A skin lesion imaged with a dermatoscope:
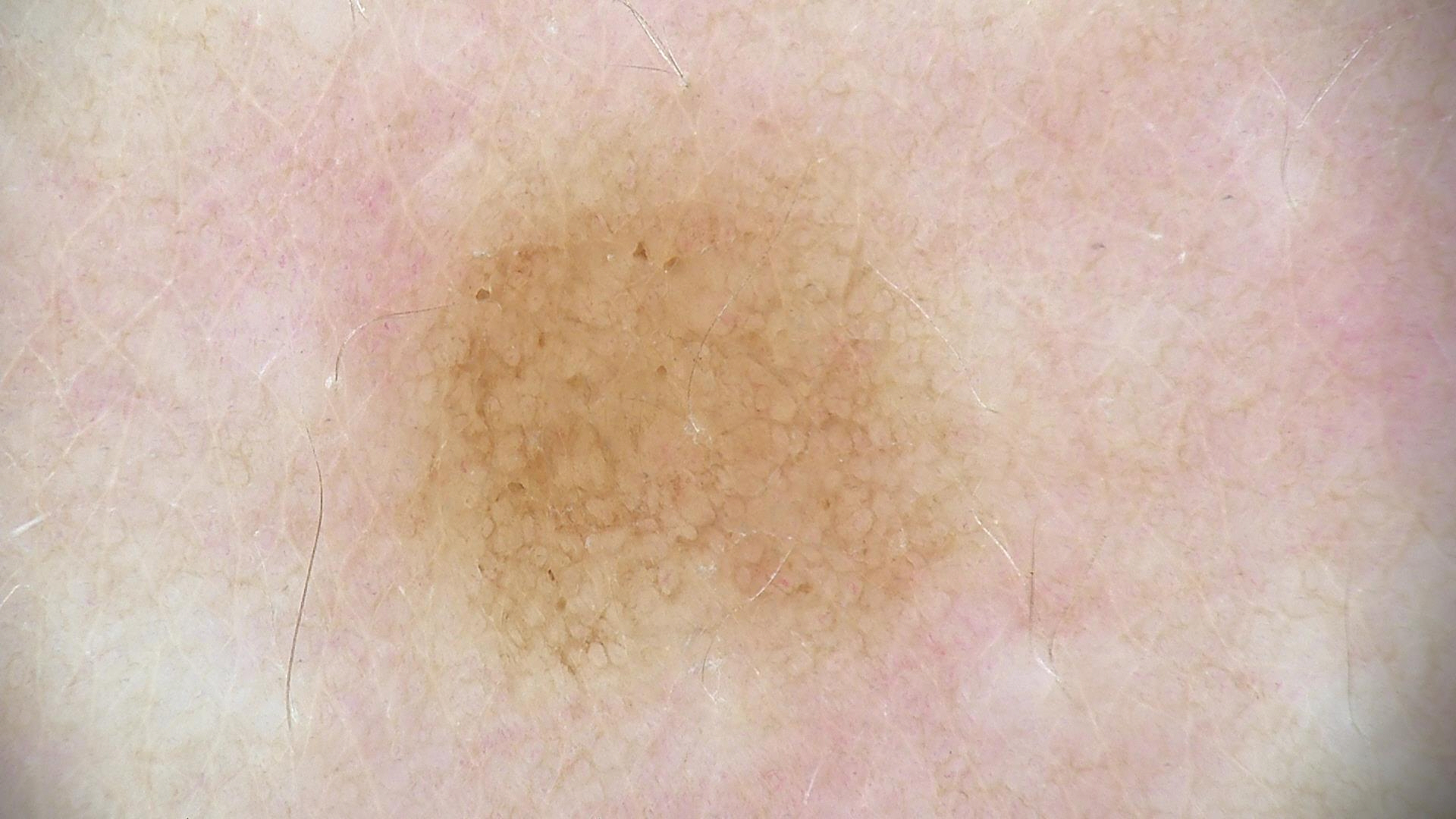Q: What is this lesion?
A: compound nevus (expert consensus)